The patient says their skin reddens with sun exposure. A female patient 27 years of age. A macroscopic clinical photograph of a skin lesion. Imaged for a research study, with no referral diagnosis recorded:
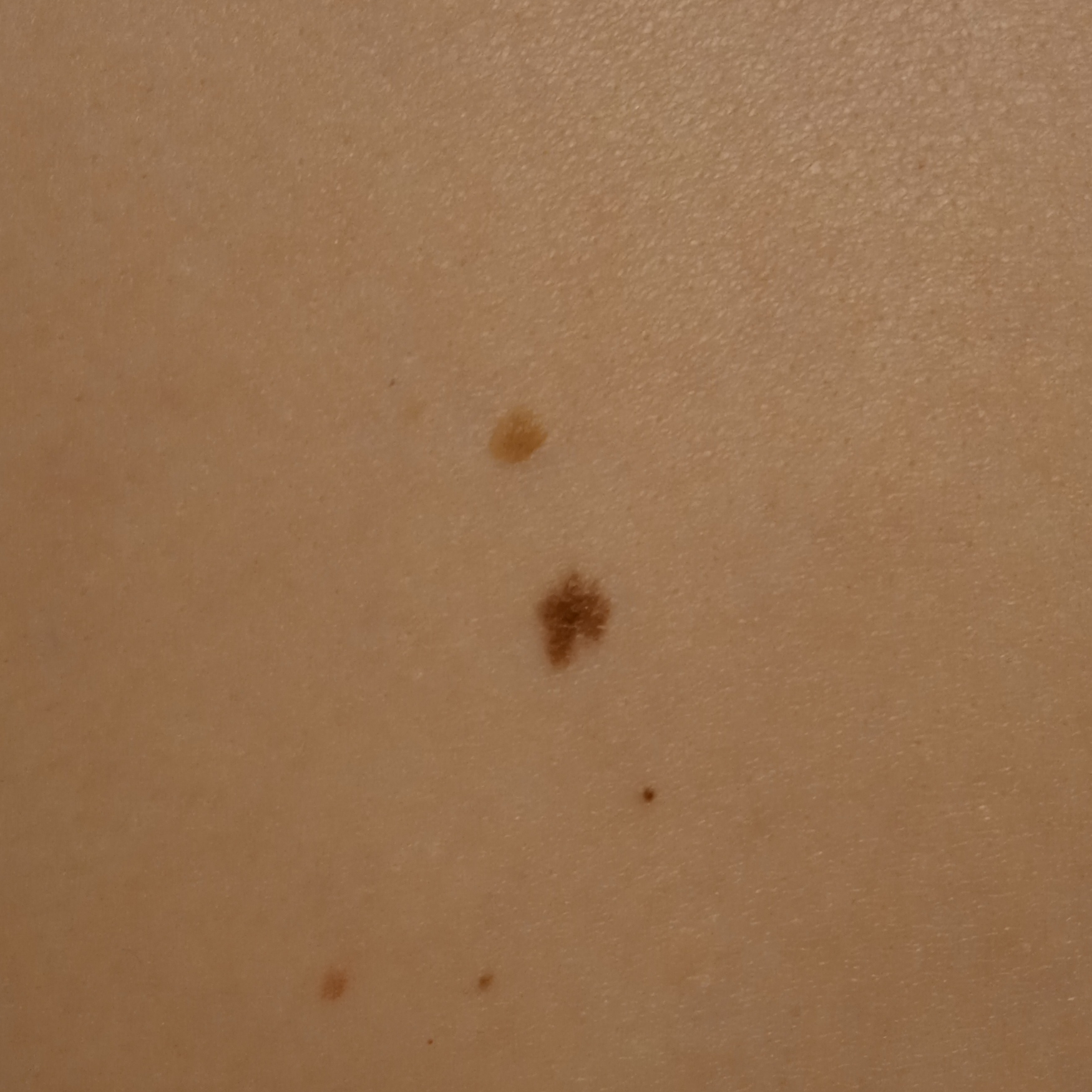Dermatologist review favored a melanocytic nevus.